The contributor reports the lesion is raised or bumpy, the patient described the issue as a rash, the lesion is associated with bothersome appearance, the arm is involved, the contributor reports the condition has been present for less than one week, this is a close-up image:
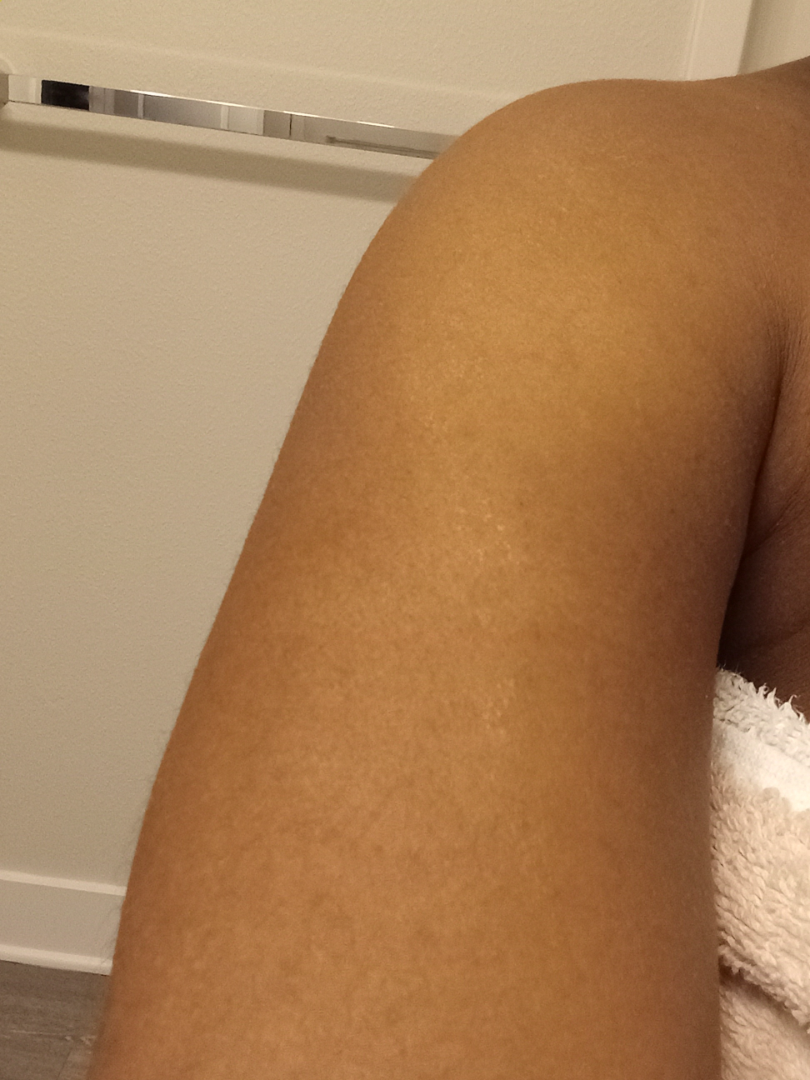Diagnostic features were not clearly distinguishable in this photograph.